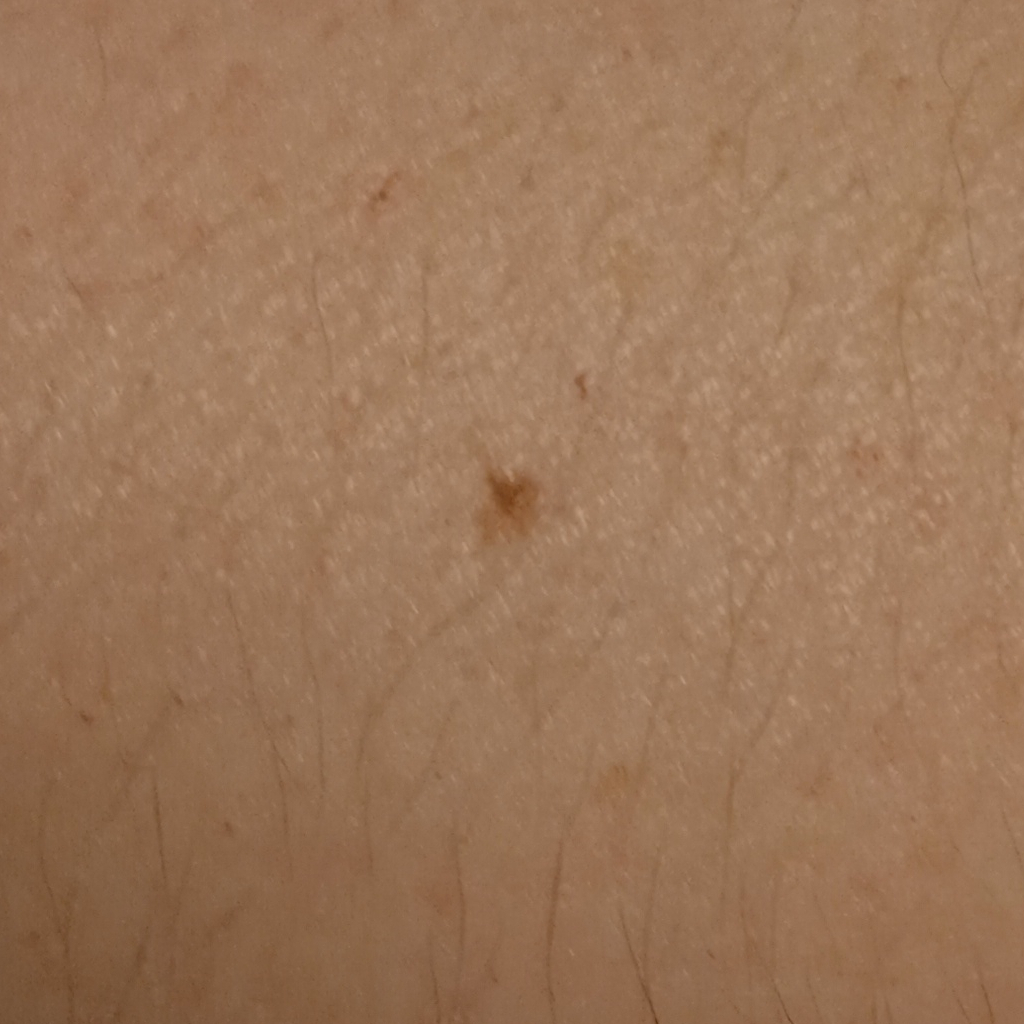A female subject 35 years of age. Collected as part of a research study, without a referral diagnosis. A clinical close-up of a skin lesion. The lesion is located on an arm. The diagnostic impression was a melanocytic nevus.